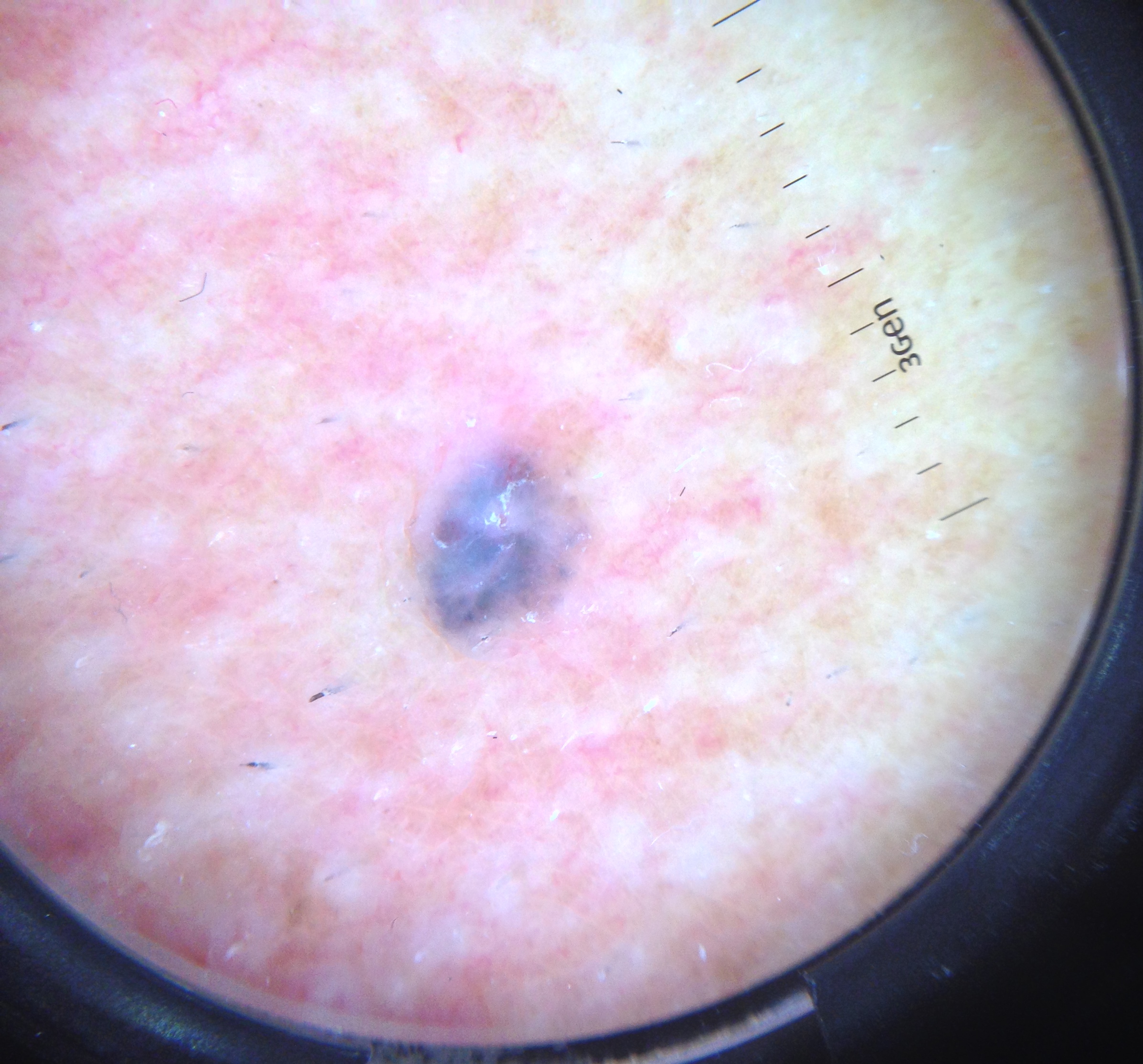Findings:
A skin lesion imaged with a dermatoscope.
Diagnosis:
Histopathology confirmed a keratinocytic lesion — a basal cell carcinoma.